A male patient 62 years old; a clinical photograph of a skin lesion; the patient was assessed as Fitzpatrick III: 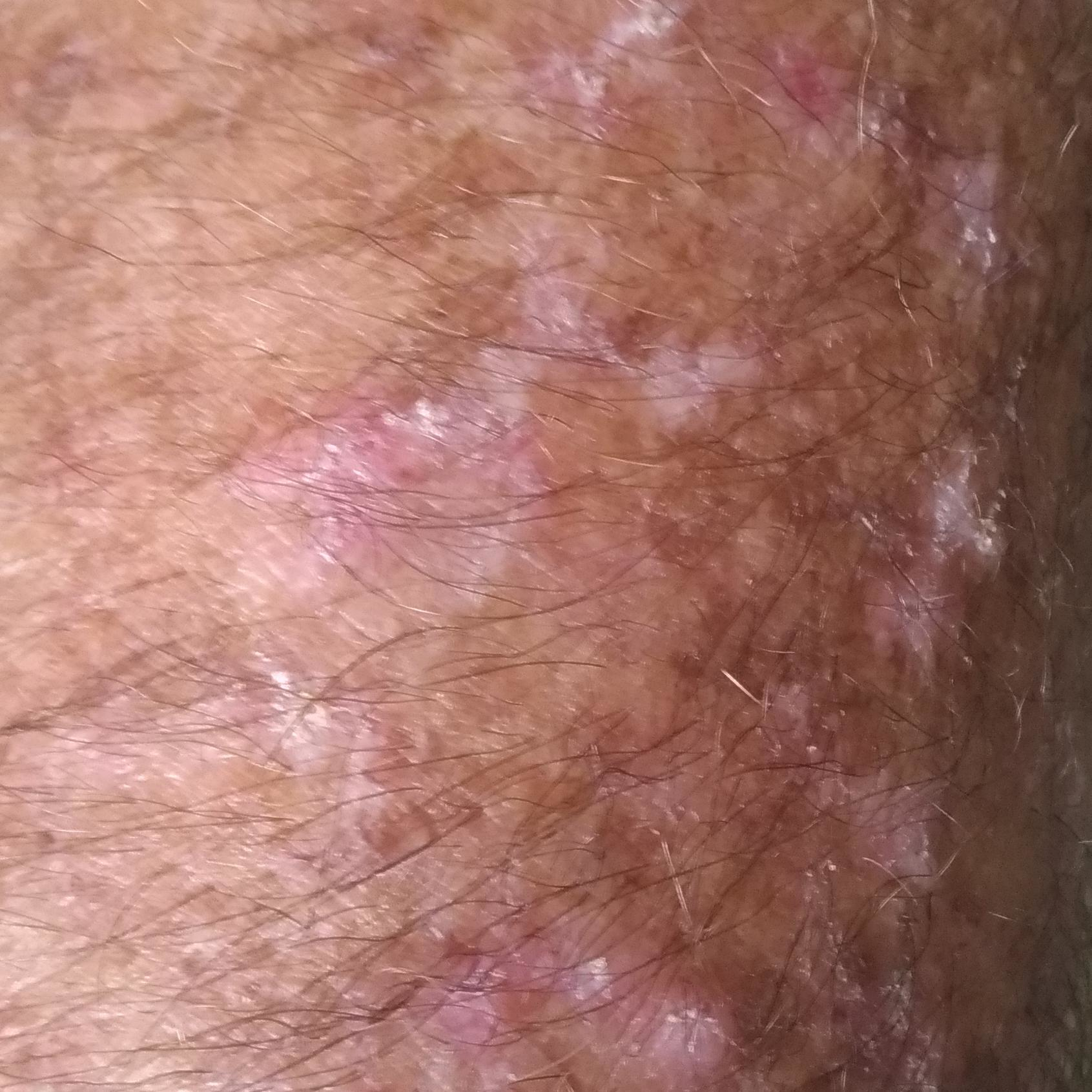Located on a forearm. The patient describes that the lesion has bled and itches. The diagnostic impression was an actinic keratosis.